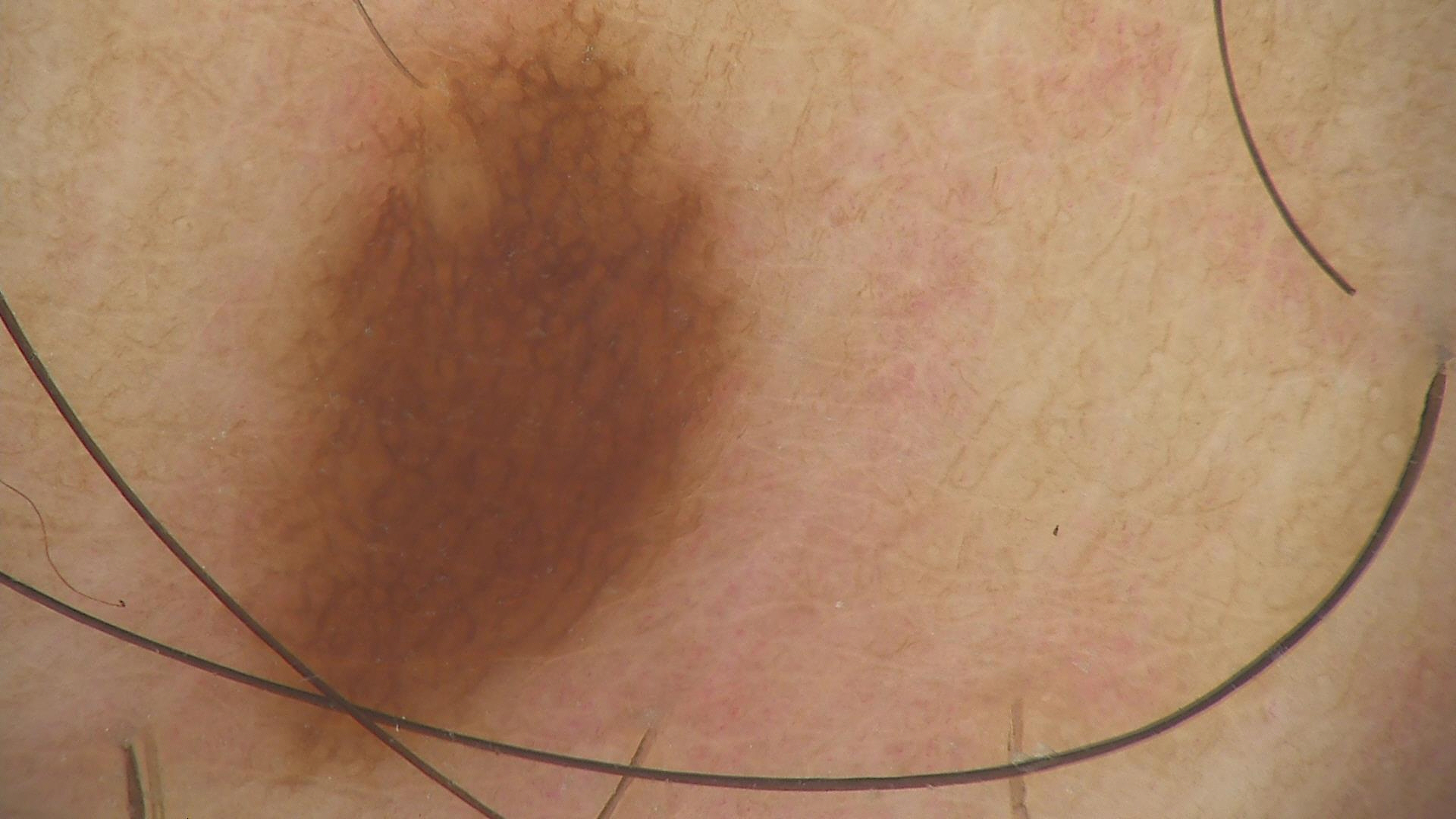Q: What is the imaging modality?
A: dermoscopy
Q: What is this lesion?
A: junctional nevus (expert consensus)